A skin lesion imaged with a dermatoscope.
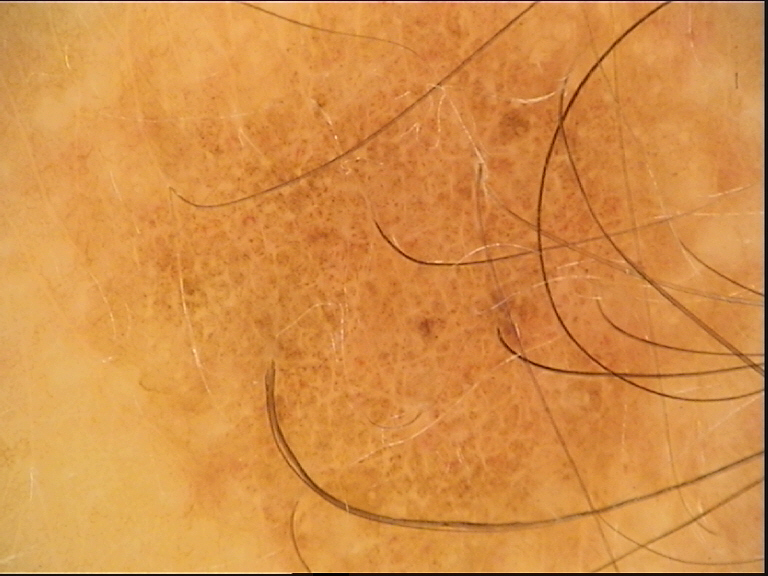The diagnosis was a dysplastic junctional nevus.